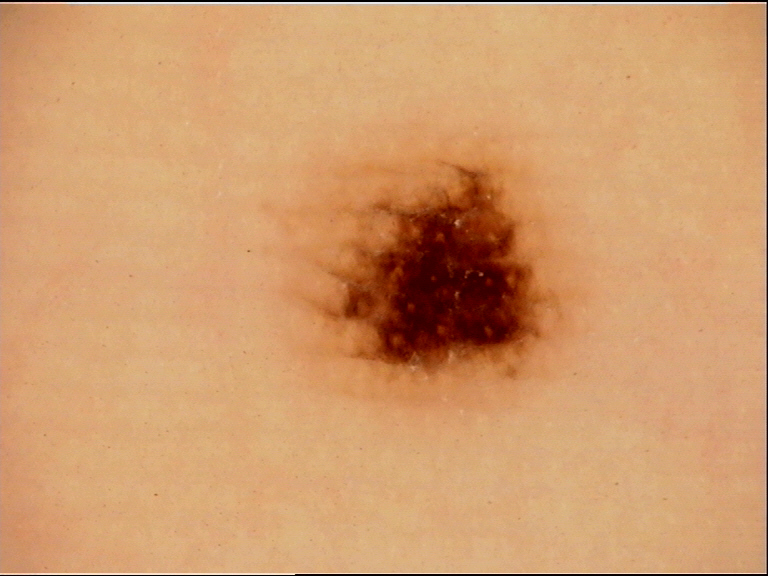category = banal, label = acral junctional nevus (expert consensus).